The photograph was taken at a distance: 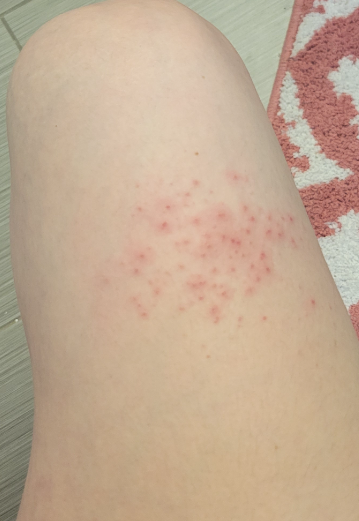The contributor reports bothersome appearance, itching and enlargement. The patient considered this a rash. The patient reported no systemic symptoms. Reported duration is one to four weeks. The reviewing panel's impression was: the differential is split between Dermatitis herpetiformis and Folliculitis.